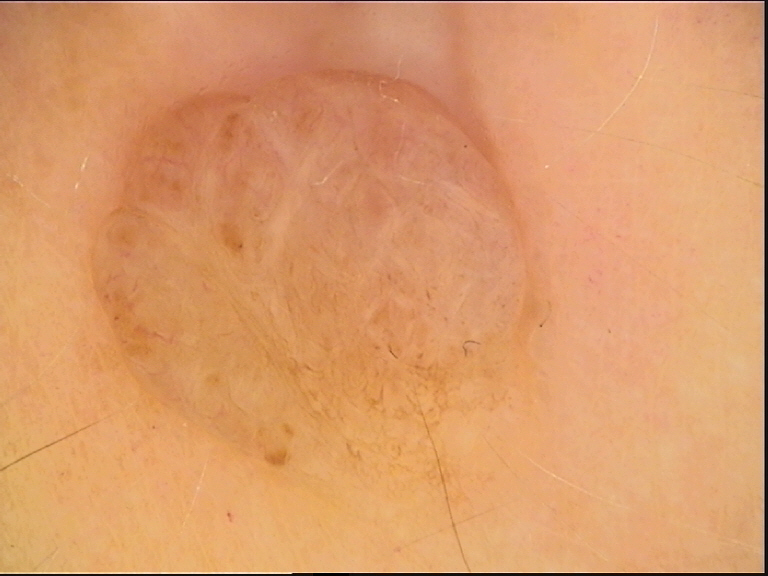{
  "diagnosis": {
    "name": "dermal nevus",
    "code": "db",
    "malignancy": "benign",
    "super_class": "melanocytic",
    "confirmation": "expert consensus"
  }
}